The photograph is a close-up of the affected area. Skin tone: Fitzpatrick skin type III:
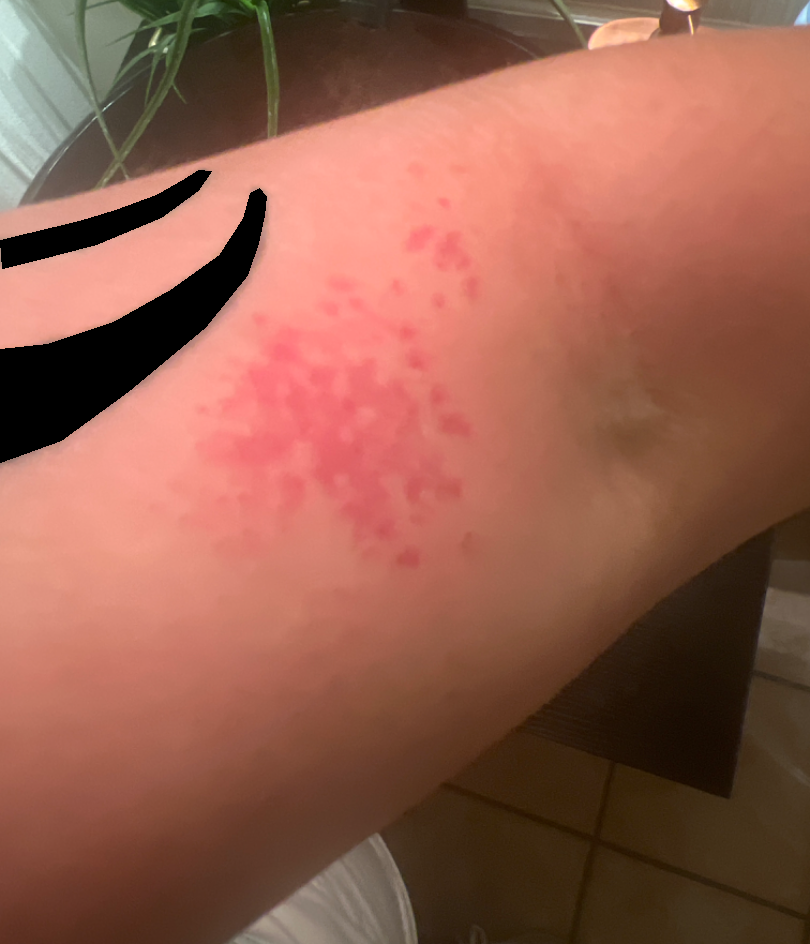A single dermatologist reviewed the case: Eczema, Allergic Contact Dermatitis and Irritant Contact Dermatitis were considered with similar weight.